An image taken at a distance · the affected area is the arm.
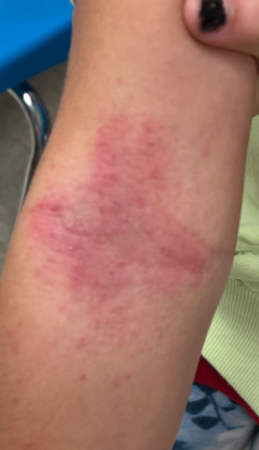Notes:
• patient-reported symptoms · itching
• skin tone · FST IV; human graders estimated Monk Skin Tone 4 or 5
• onset · one to four weeks
• surface texture · rough or flaky
• dermatologist impression · in keeping with Eczema